A dermoscopic close-up of a skin lesion.
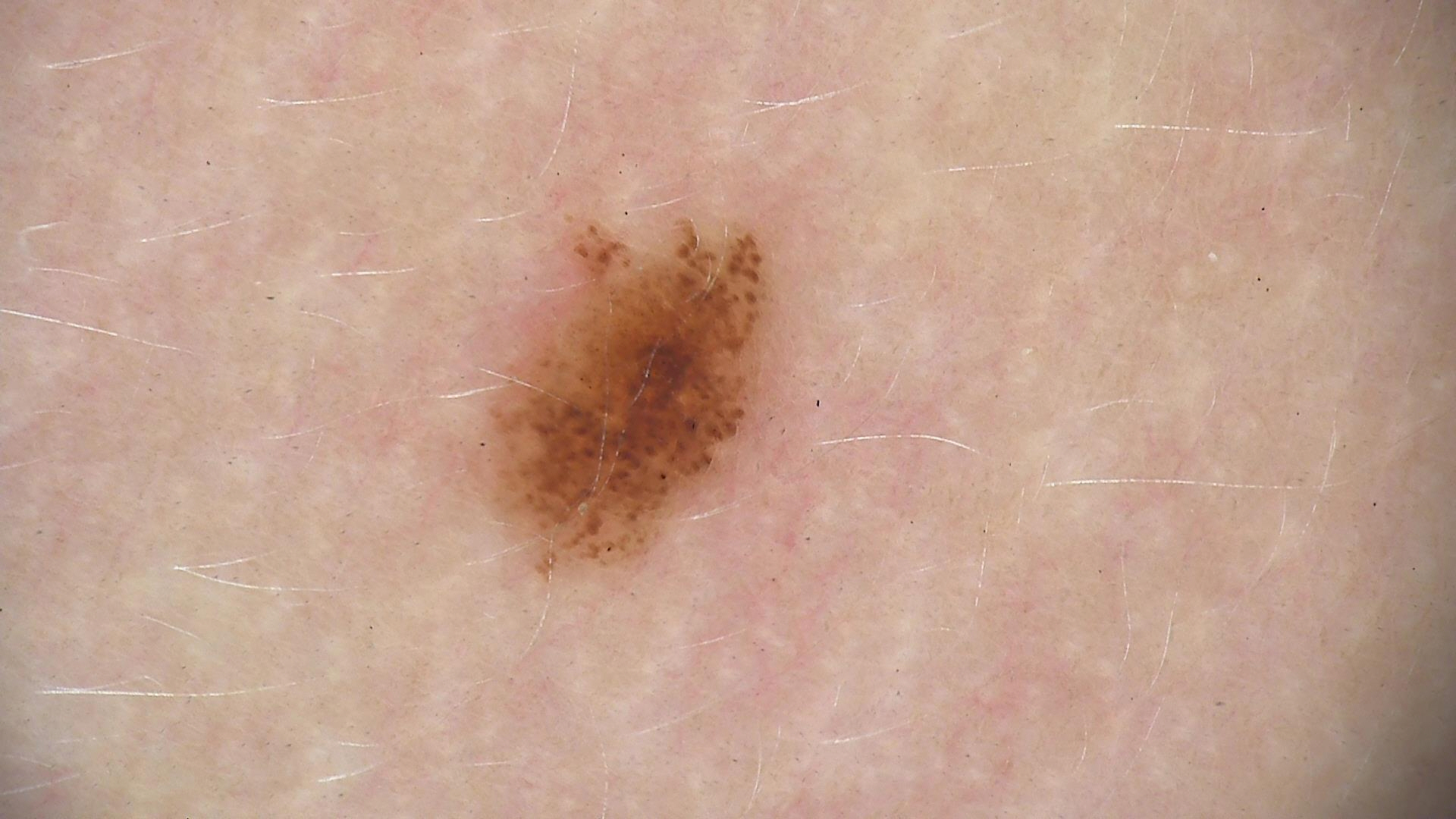Diagnosed as a benign lesion — a dysplastic junctional nevus.